No relevant systemic symptoms. The contributor notes bleeding and burning. Fitzpatrick skin type II. The patient considered this a rash. A close-up photograph. The condition has been present for about one day. The subject is a female aged 18–29. The contributor notes the lesion is rough or flaky and raised or bumpy:
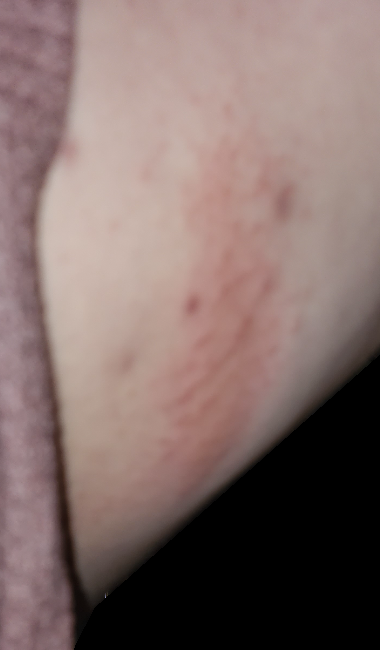differential:
  leading:
    - Contact dermatitis
  considered:
    - Eczema
    - Allergic Contact Dermatitis